Dermoscopy of a skin lesion.
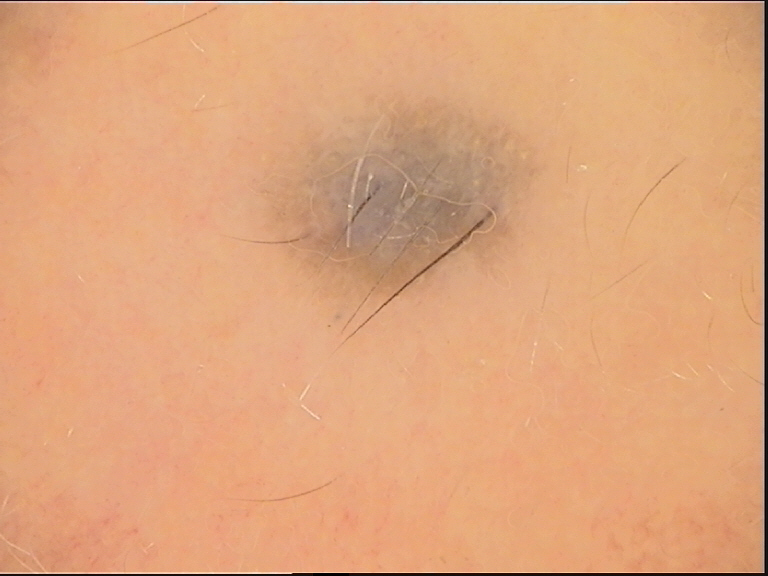<case>
<lesion_type>
<main_class>banal</main_class>
<pattern>dermal</pattern>
</lesion_type>
<diagnosis>
<name>blue nevus</name>
<code>bdb</code>
<malignancy>benign</malignancy>
<super_class>melanocytic</super_class>
<confirmation>expert consensus</confirmation>
</diagnosis>
</case>